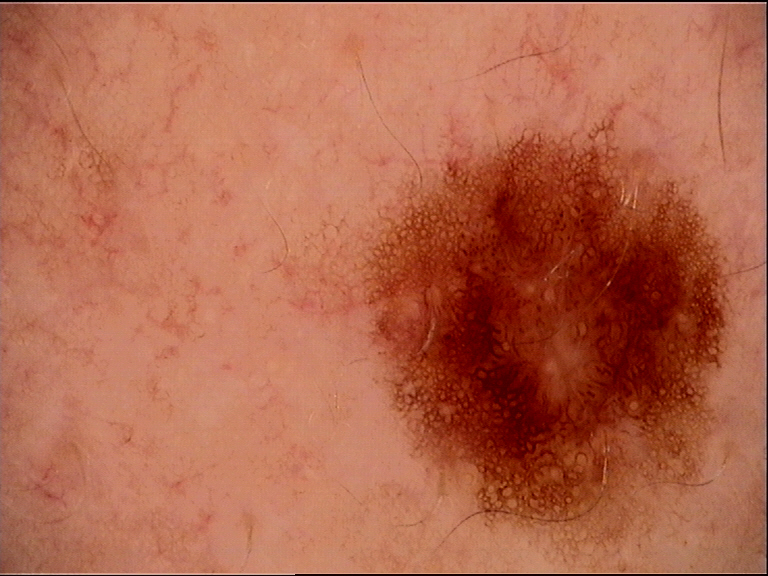The diagnosis was a dysplastic junctional nevus.